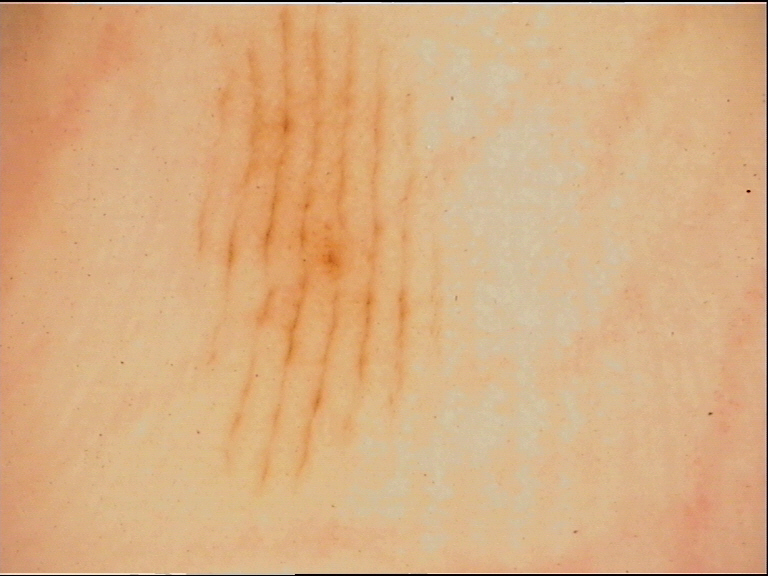{
  "image": "dermatoscopy",
  "diagnosis": {
    "name": "acral junctional nevus",
    "code": "ajb",
    "malignancy": "benign",
    "super_class": "melanocytic",
    "confirmation": "expert consensus"
  }
}